A skin lesion imaged with a dermatoscope.
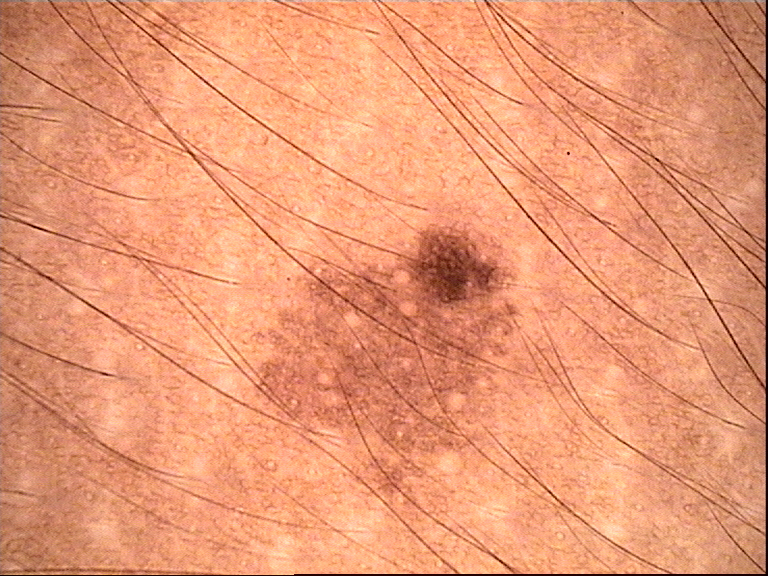Impression: The diagnosis was a dysplastic junctional nevus.